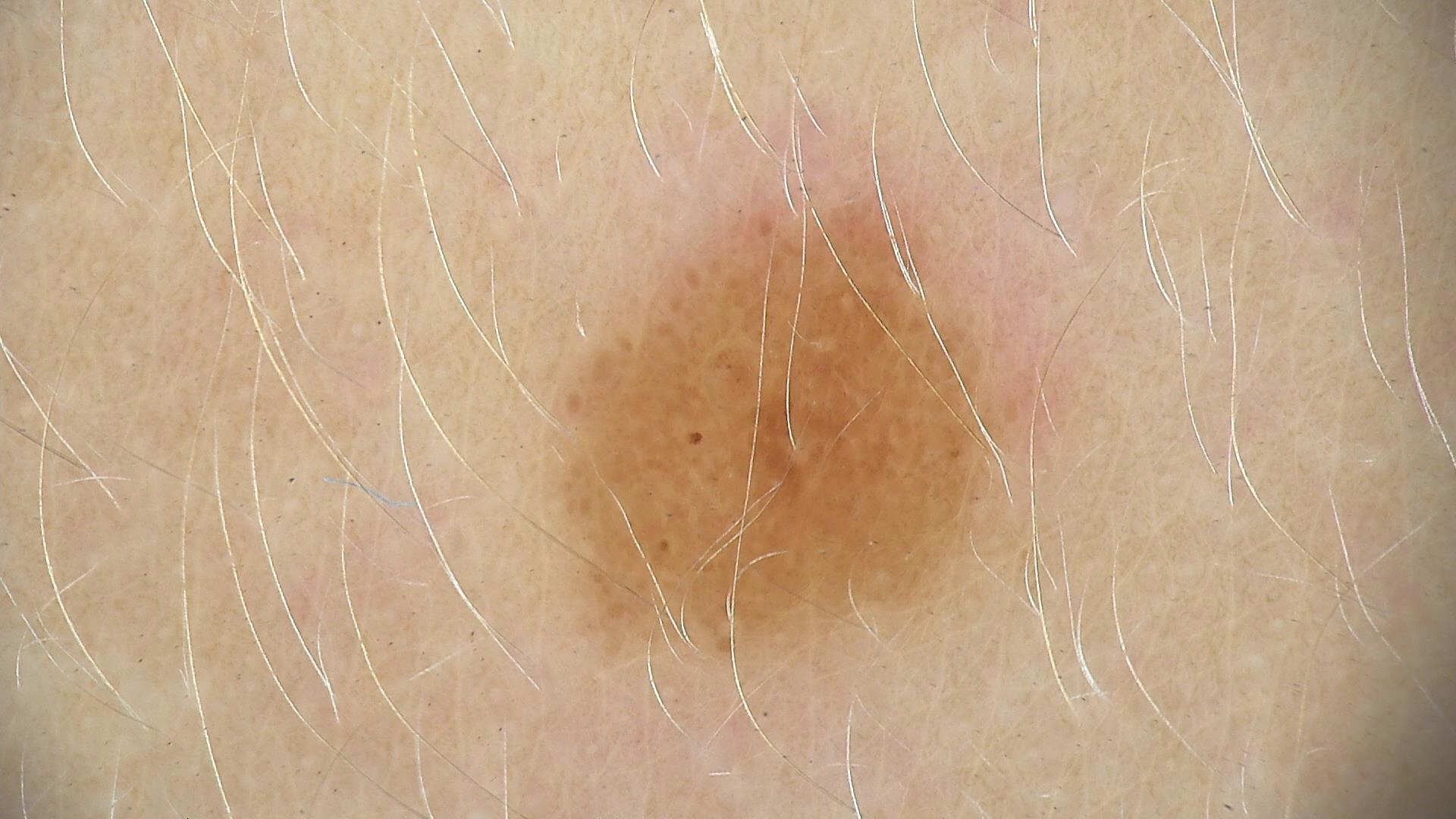The diagnostic label was a dysplastic junctional nevus.